The patient described the issue as a rash · the arm is involved · this image was taken at an angle · texture is reported as fluid-filled and raised or bumpy · present for one to four weeks · no associated systemic symptoms reported · reported lesion symptoms include itching, bothersome appearance and enlargement · the subject is a male aged 18–29: 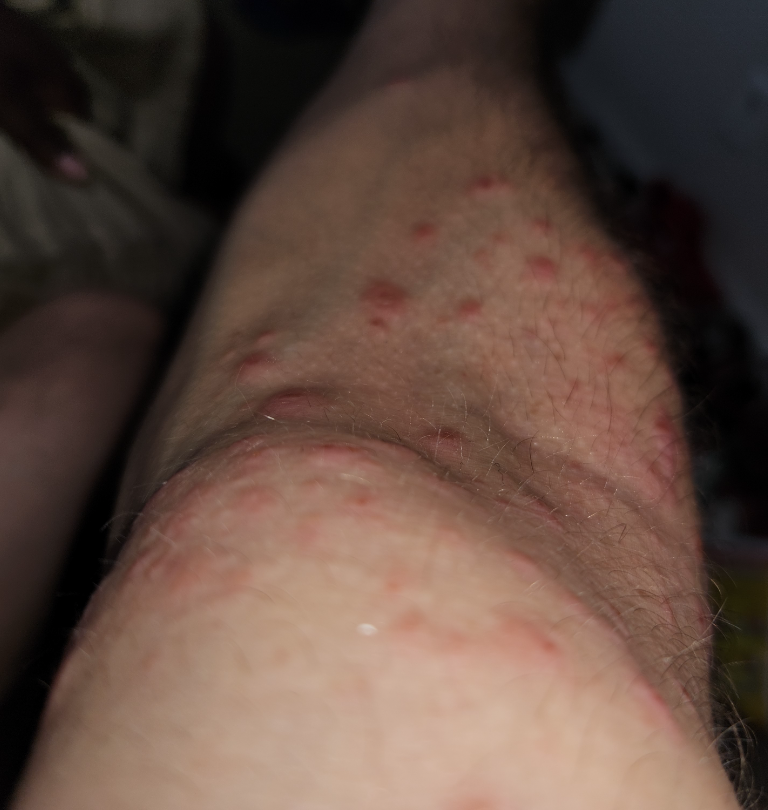– impression · Viral Exanthem (primary); Scabies (possible); Eczema (less likely)